A dermoscopy image of a single skin lesion.
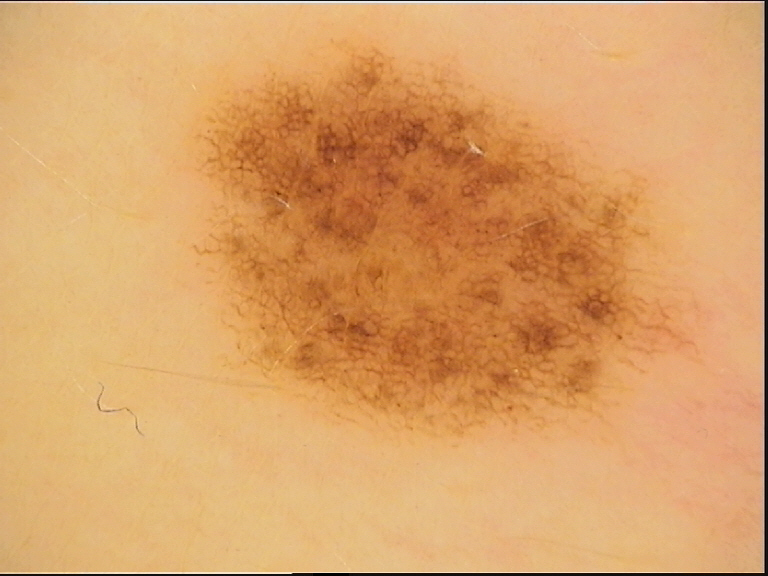{
  "diagnosis": {
    "name": "dysplastic junctional nevus",
    "code": "jd",
    "malignancy": "benign",
    "super_class": "melanocytic",
    "confirmation": "expert consensus"
  }
}